An image taken at a distance, located on the head or neck:
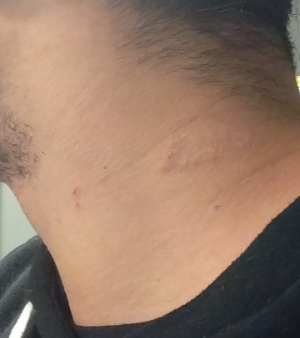Impression: No differential diagnosis could be assigned on photographic review. History: Texture is reported as raised or bumpy and rough or flaky. Reported duration is one to four weeks. Fitzpatrick skin type IV; lay reviewers estimated Monk Skin Tone 3–4. Self-categorized by the patient as a rash. The lesion is associated with itching and enlargement.